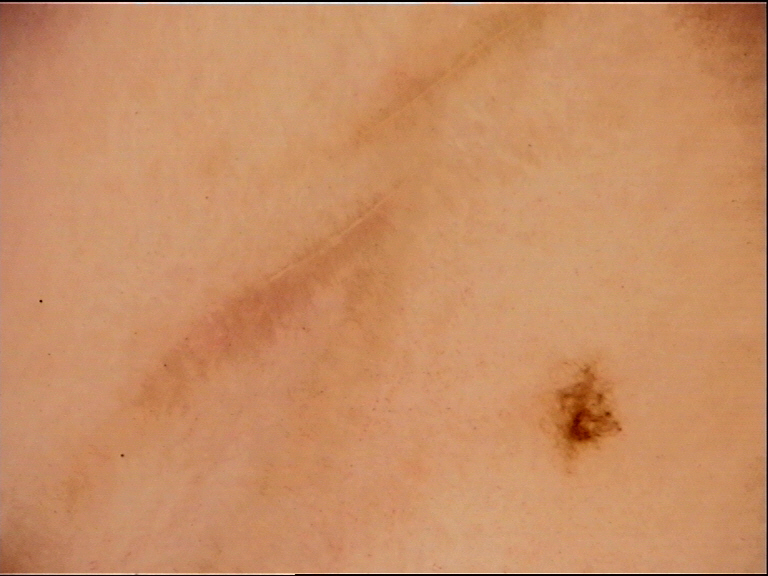Conclusion: Consistent with an acral dysplastic junctional nevus.